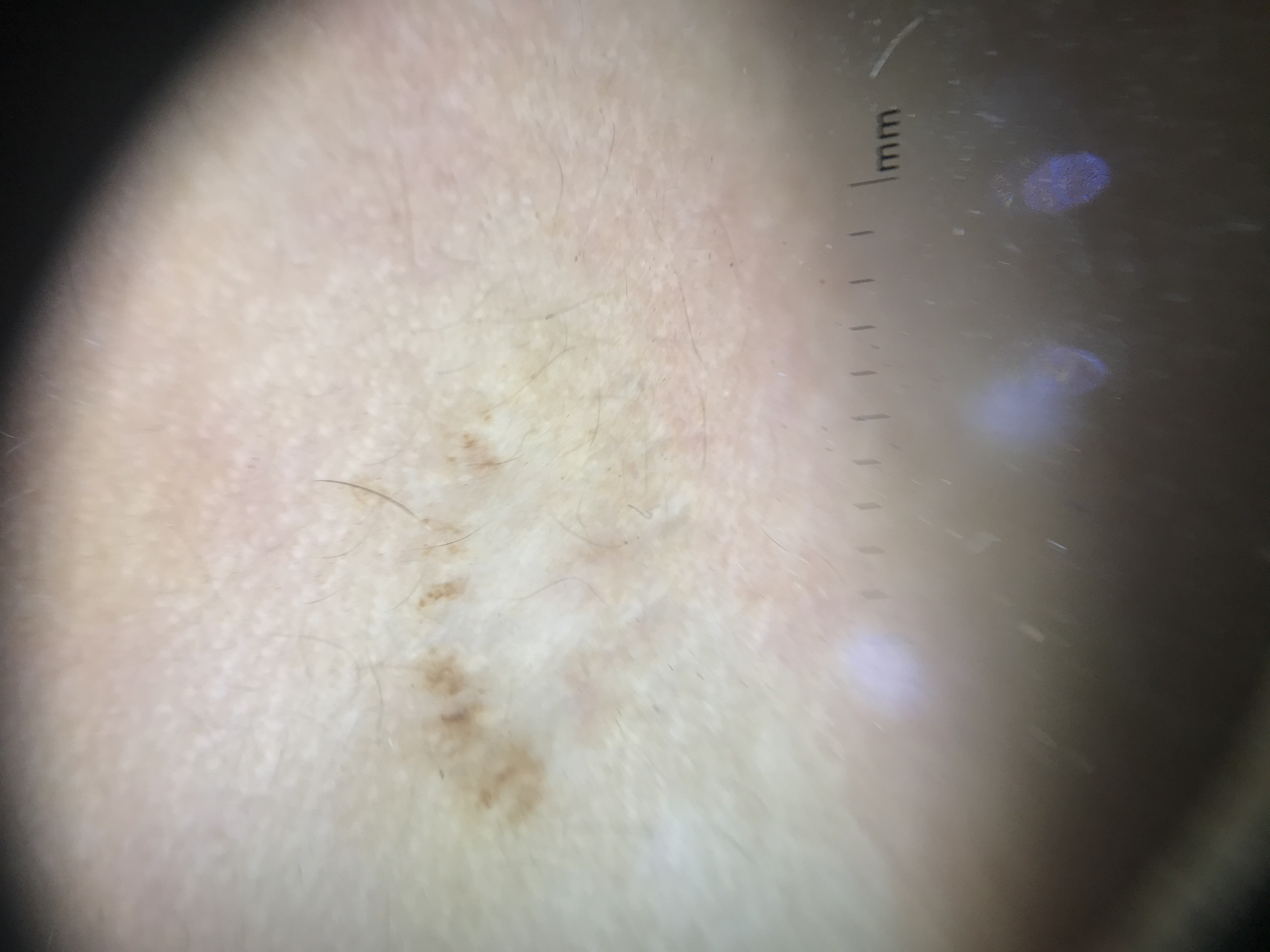Q: What kind of image is this?
A: dermoscopy
Q: What is this lesion?
A: recurrent nevus (expert consensus)